A skin lesion imaged with contact-polarized dermoscopy; the chart documents a previous melanoma but no melanoma in first-degree relatives; the patient was assessed as Fitzpatrick phototype II; a female subject aged approximately 75.
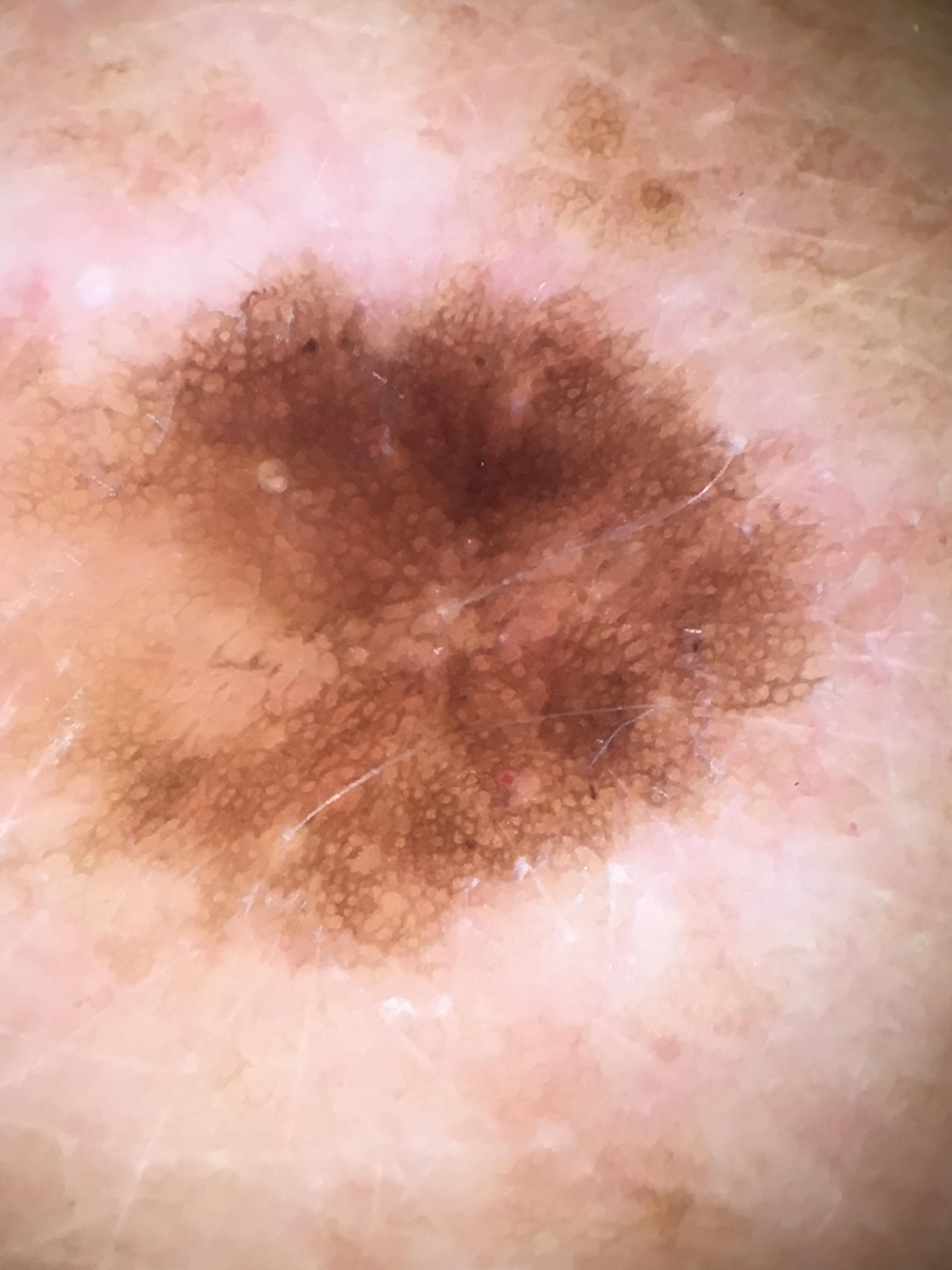site=the posterior trunk; pathology=Nevus (biopsy-proven).